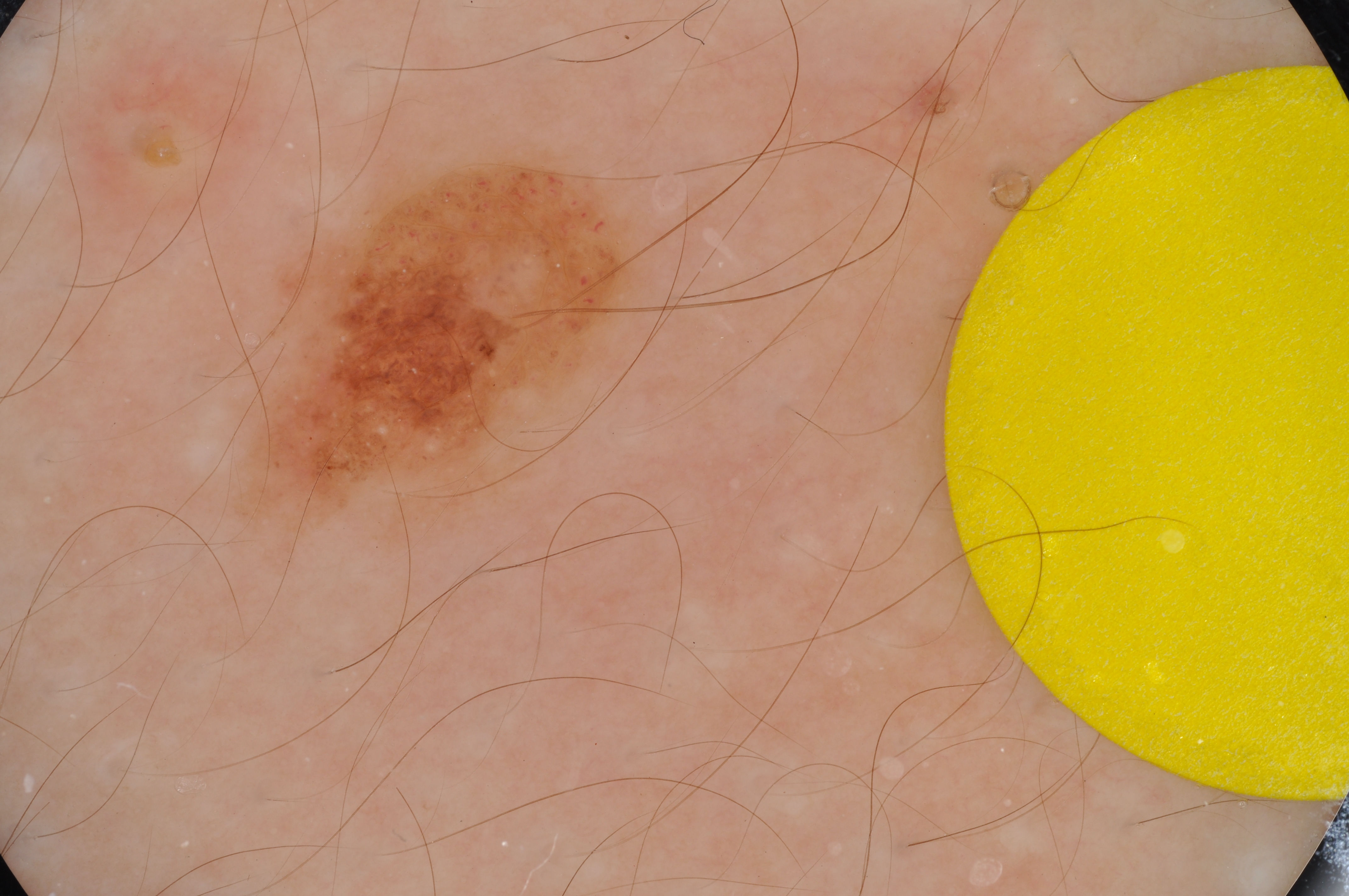Notes:
* modality — dermoscopic image
* subject — male, aged 13 to 17
* location — (237, 156, 637, 540)
* dermoscopic features — milia-like cysts; absent: streaks, globules, negative network, and pigment network
* assessment — a melanocytic nevus